The lesion involves the top or side of the foot and leg; the contributor reports the lesion is rough or flaky; no associated systemic symptoms reported; present for three to twelve months; the subject is 50–59, female; the lesion is associated with bothersome appearance, pain and itching; this is a close-up image:
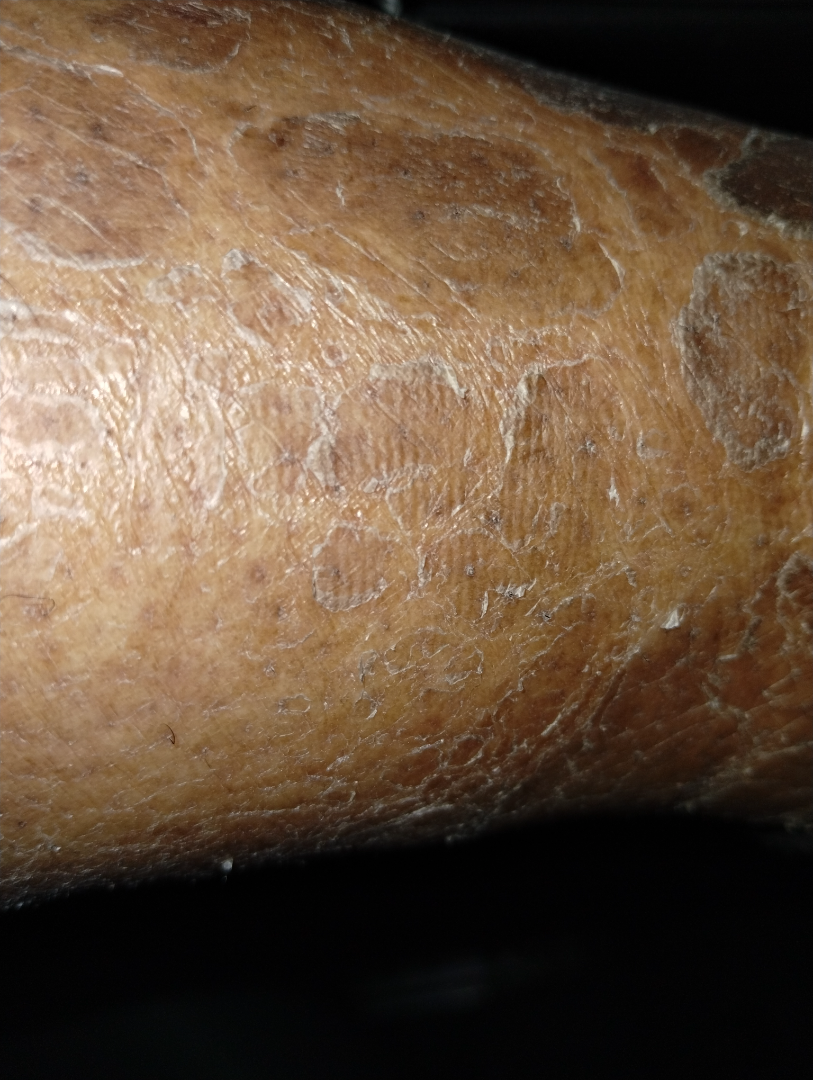{
  "differential": {
    "Xerosis": 0.41,
    "Ichthyosis": 0.41,
    "Psoriasis": 0.18
  }
}